A skin lesion imaged with a dermatoscope.
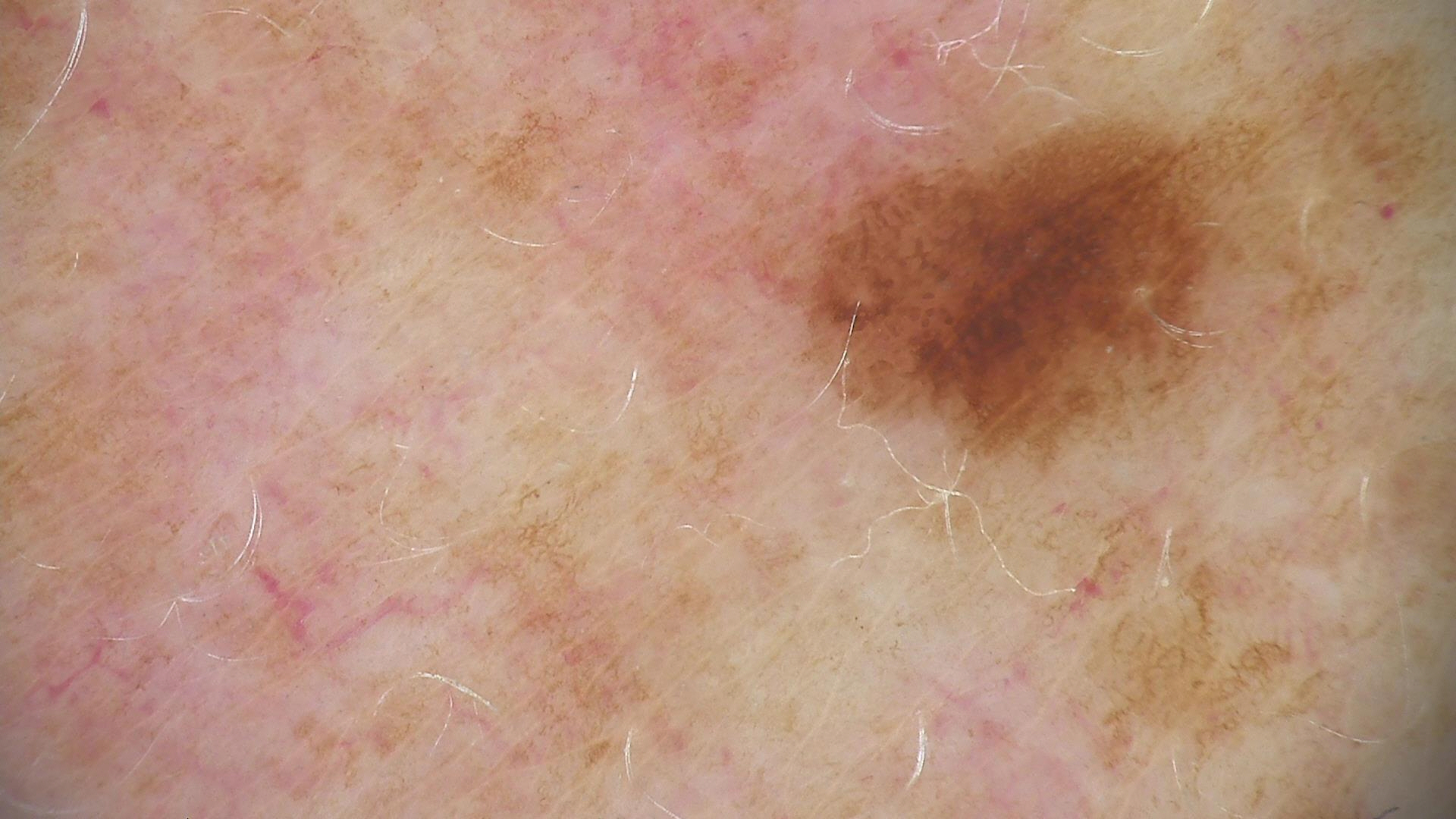  diagnosis:
    name: dysplastic junctional nevus
    code: jd
    malignancy: benign
    super_class: melanocytic
    confirmation: expert consensus